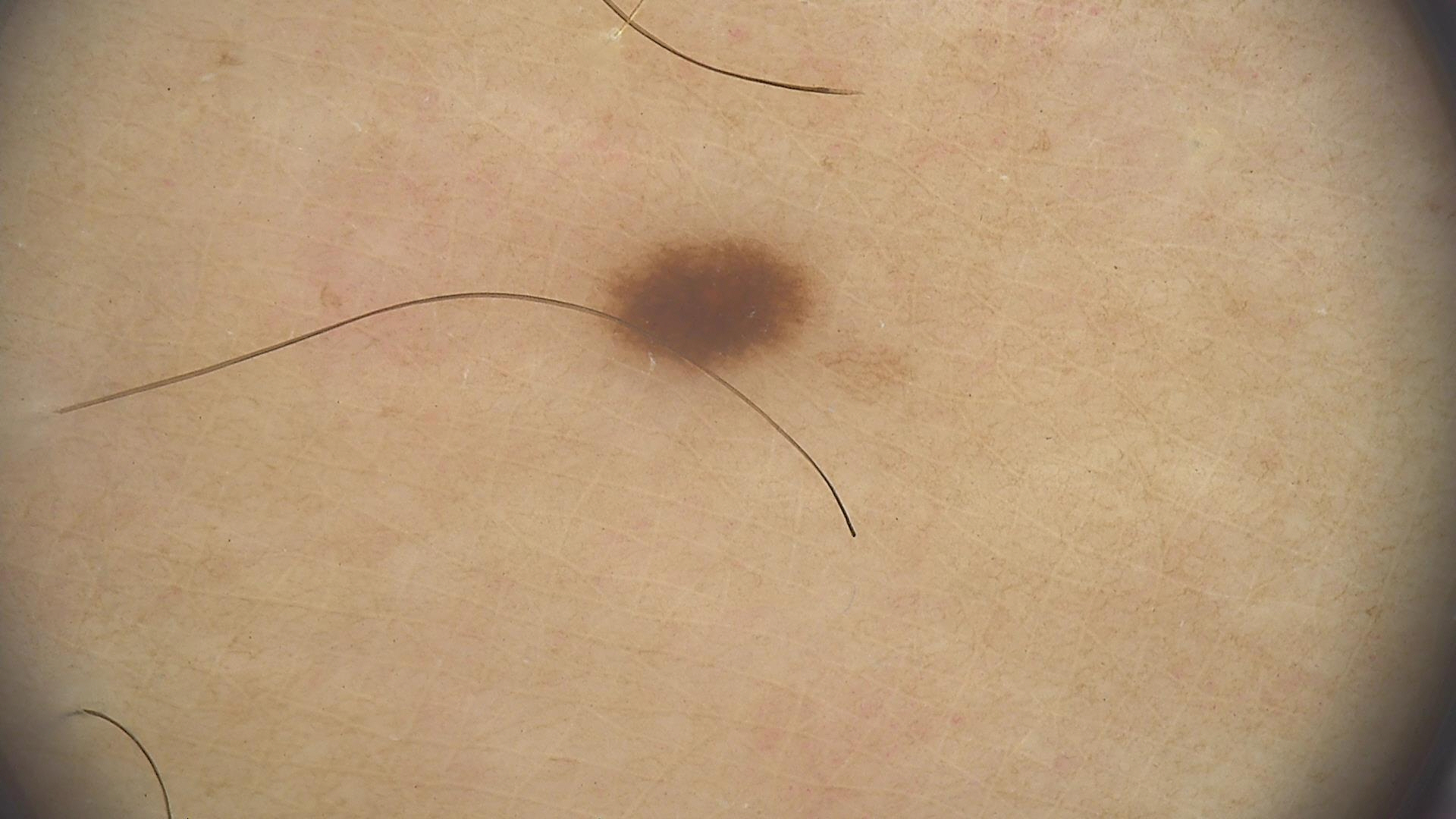| feature | finding |
|---|---|
| imaging | dermatoscopy |
| classification | banal |
| assessment | junctional nevus (expert consensus) |